Self-categorized by the patient as a rash. A close-up photograph.
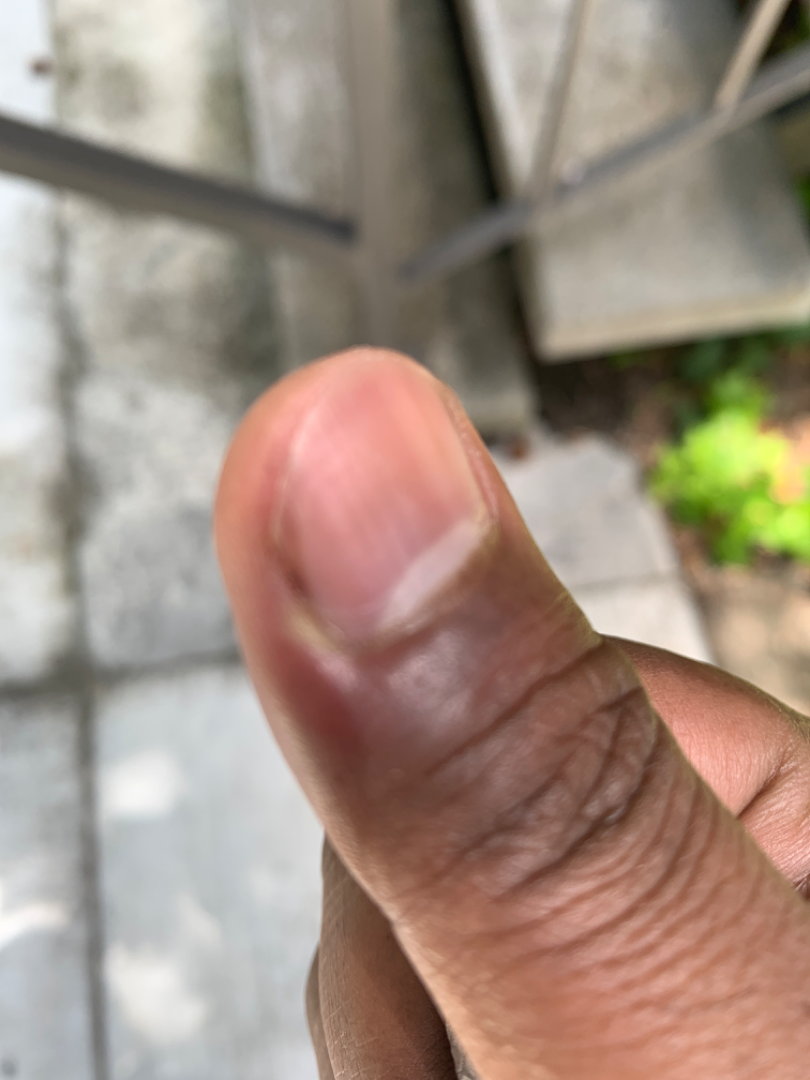Paronychia (leading); Herpes Simplex (considered); Eczema (considered).